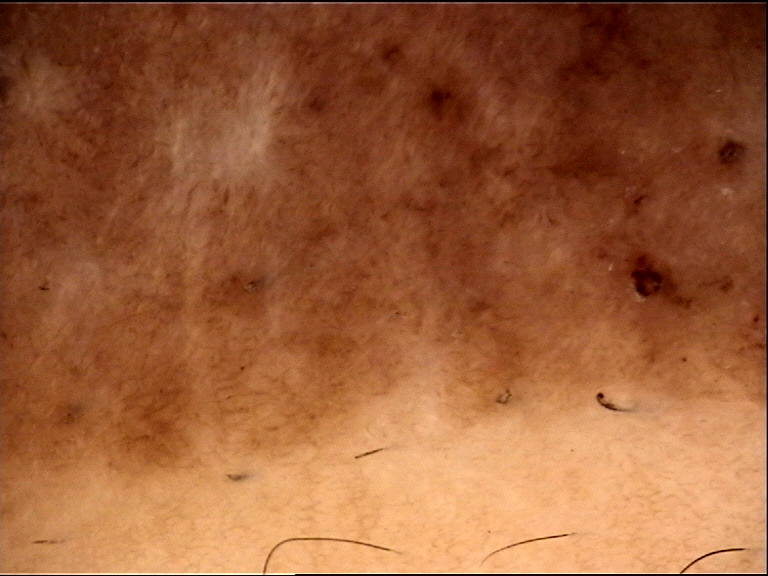Conclusion: Diagnosed as a congenital compound nevus.